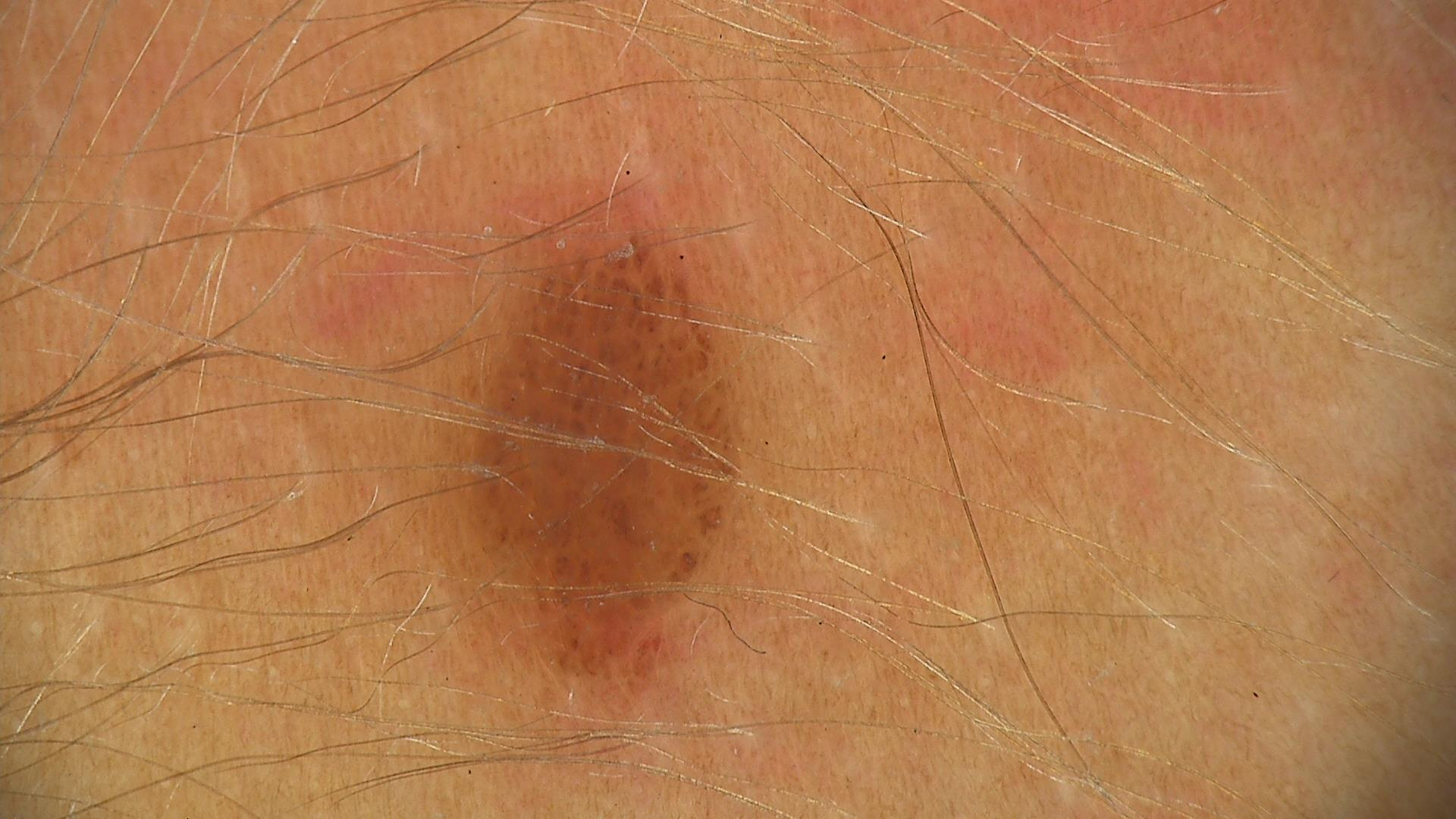Case:
The morphology is that of a banal lesion.
Conclusion:
Consistent with a compound nevus.